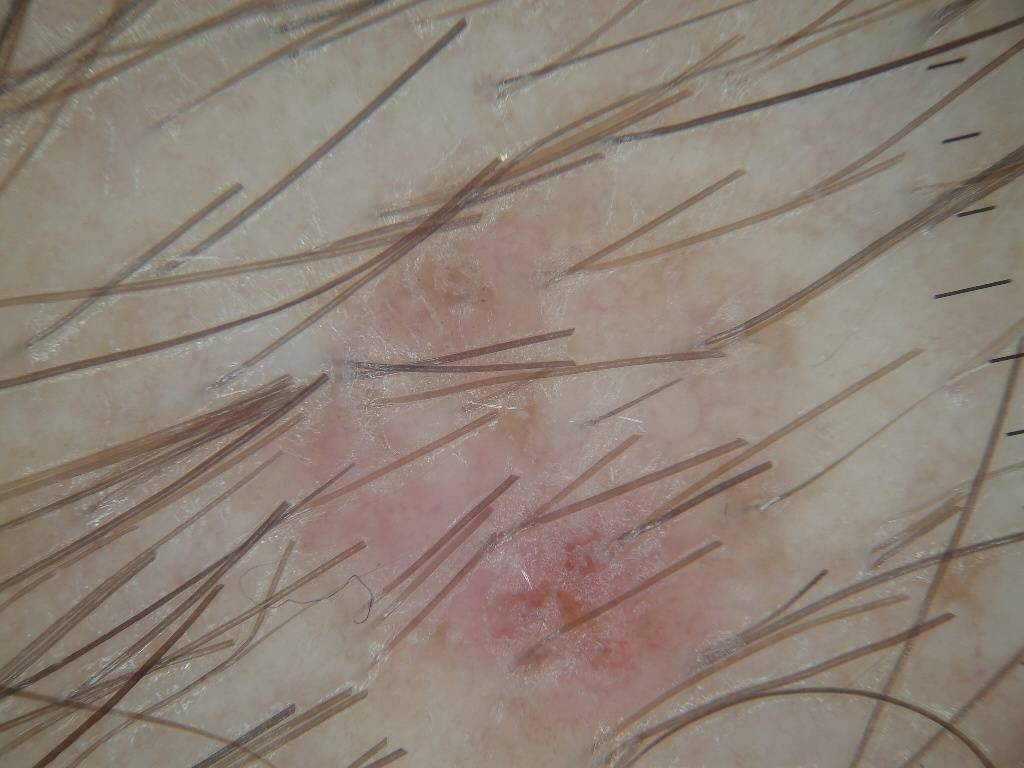A dermoscopic image of a skin lesion.
In (x1, y1, x2, y2) order, the lesion spans [276, 139, 832, 747].
The lesion takes up about 33% of the image.
Clinically diagnosed as a benign lesion.